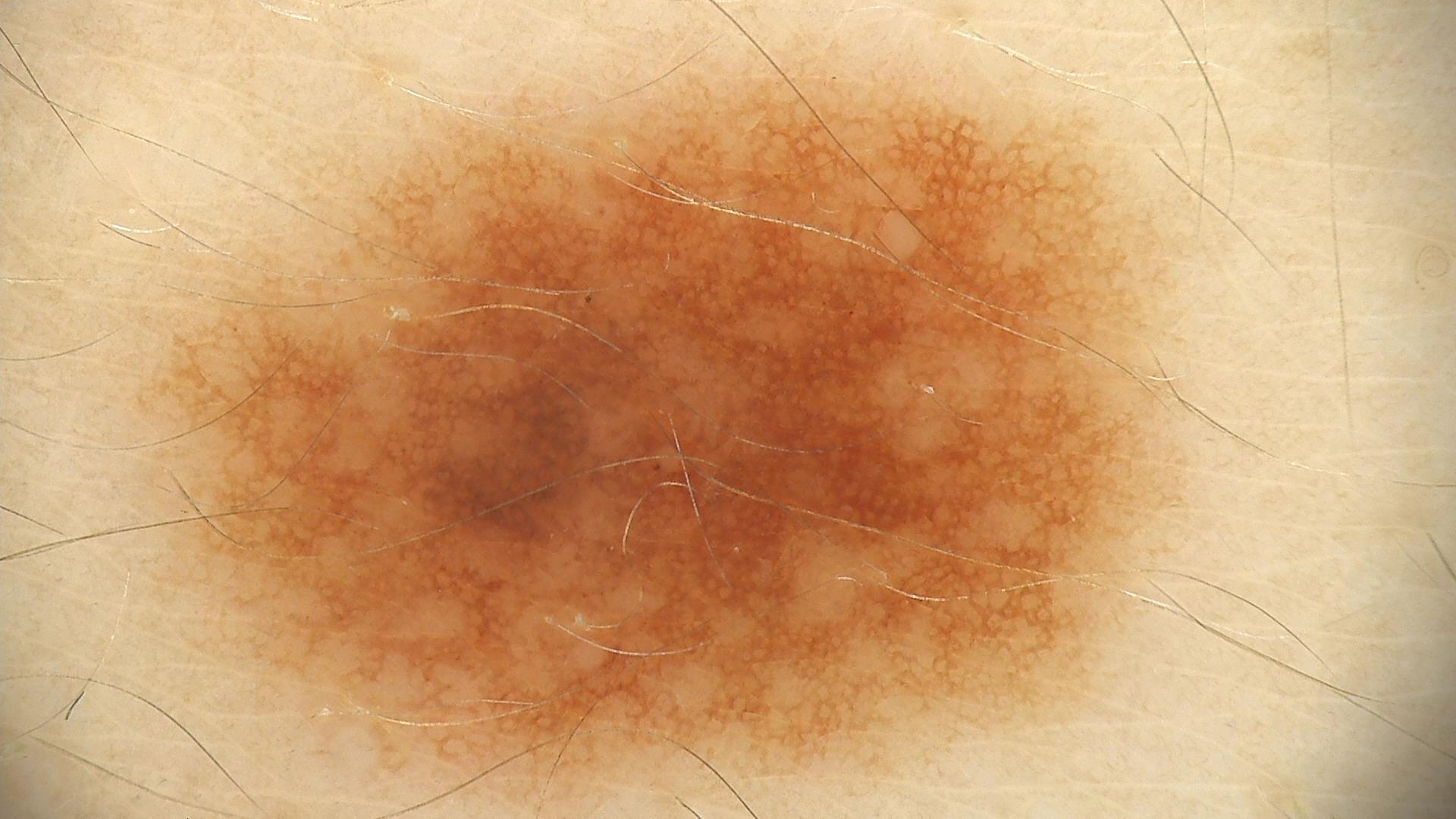Findings:
- image: dermatoscopy
- label: dysplastic junctional nevus (expert consensus)